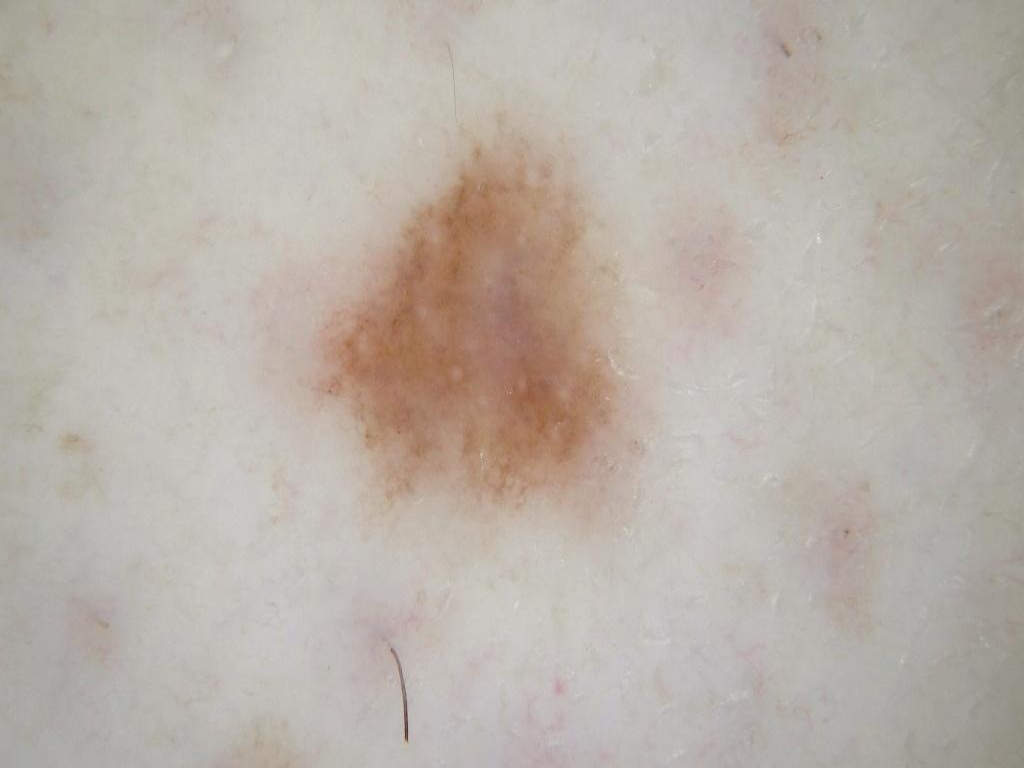A dermoscopy image of a single skin lesion. On dermoscopy, the lesion shows pigment network, with no streaks, milia-like cysts, negative network, or globules. In (x1, y1, x2, y2) order, the lesion occupies the region box(290, 106, 642, 530). The lesion was assessed as a melanocytic nevus, a benign lesion.